The photograph was taken at an angle. The front of the torso and arm are involved: 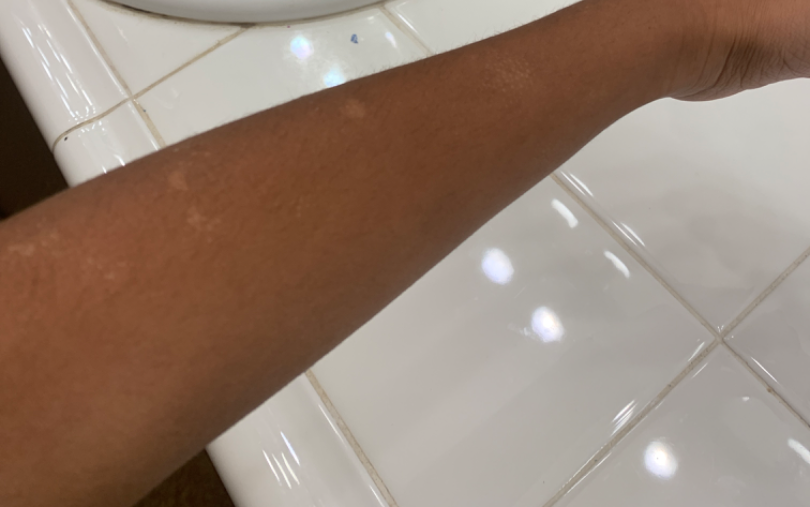Impression: The reviewing dermatologist was unable to assign a differential diagnosis from the image. History: The patient did not report lesion symptoms. The patient described the issue as a pigmentary problem.